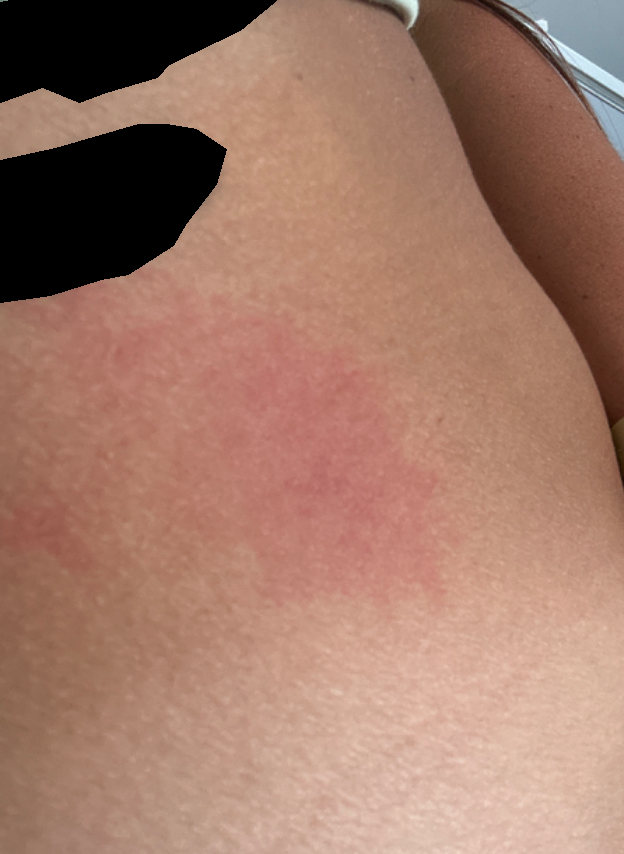{
  "assessment": "could not be assessed",
  "symptoms": "itching",
  "duration": "less than one week",
  "patient_category": "a rash",
  "systemic_symptoms": "none reported",
  "texture": "raised or bumpy",
  "shot_type": "at an angle",
  "skin_tone": {
    "fitzpatrick": "IV"
  },
  "body_site": "front of the torso"
}